A dermatoscopic image of a skin lesion — 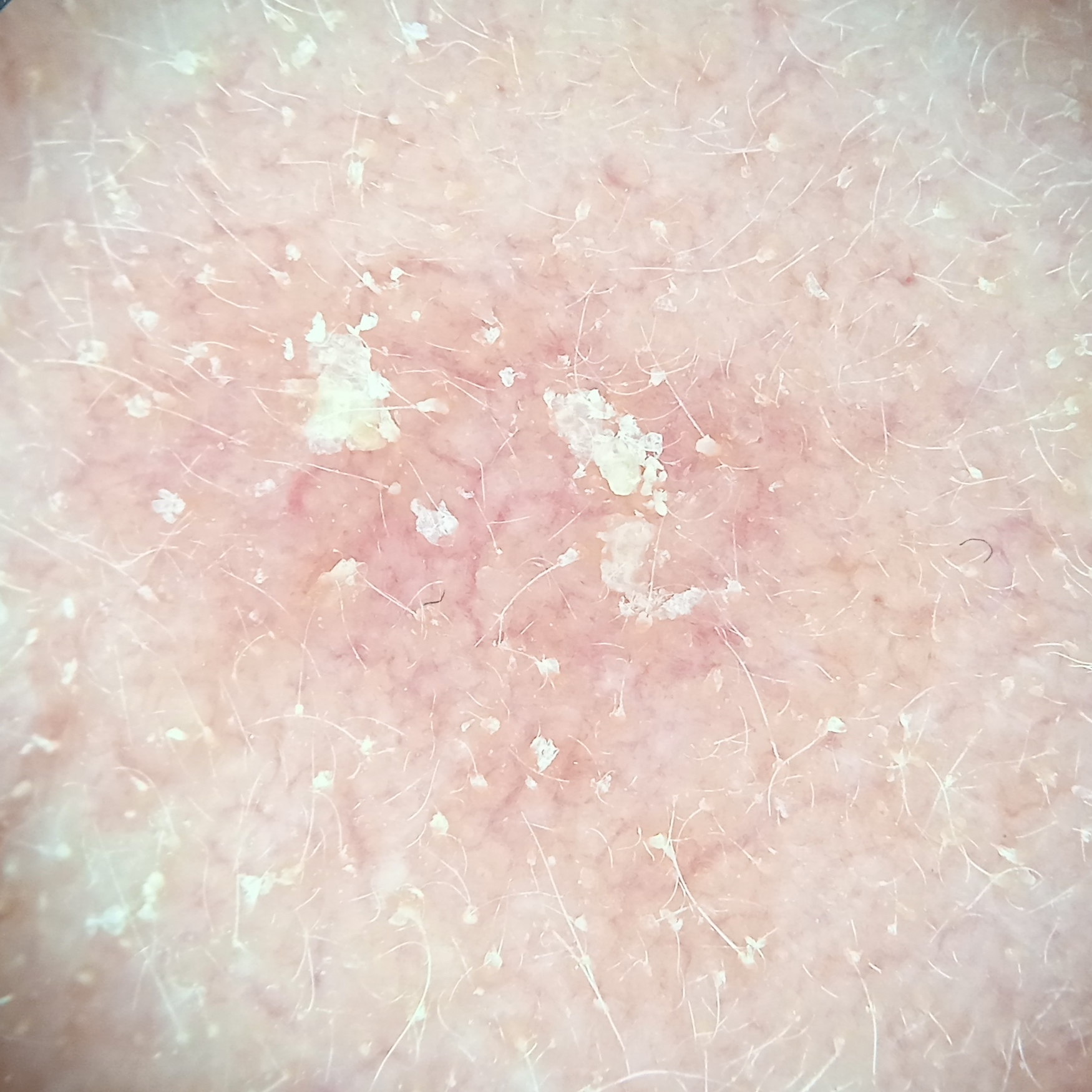lesion_location: the face
diagnosis:
  name: actinic keratosis
  malignancy: benign